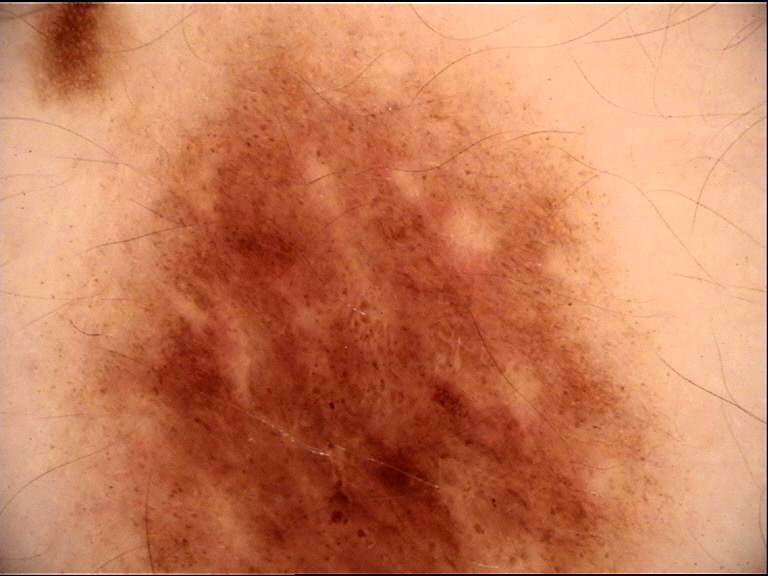Consistent with a dysplastic compound nevus.